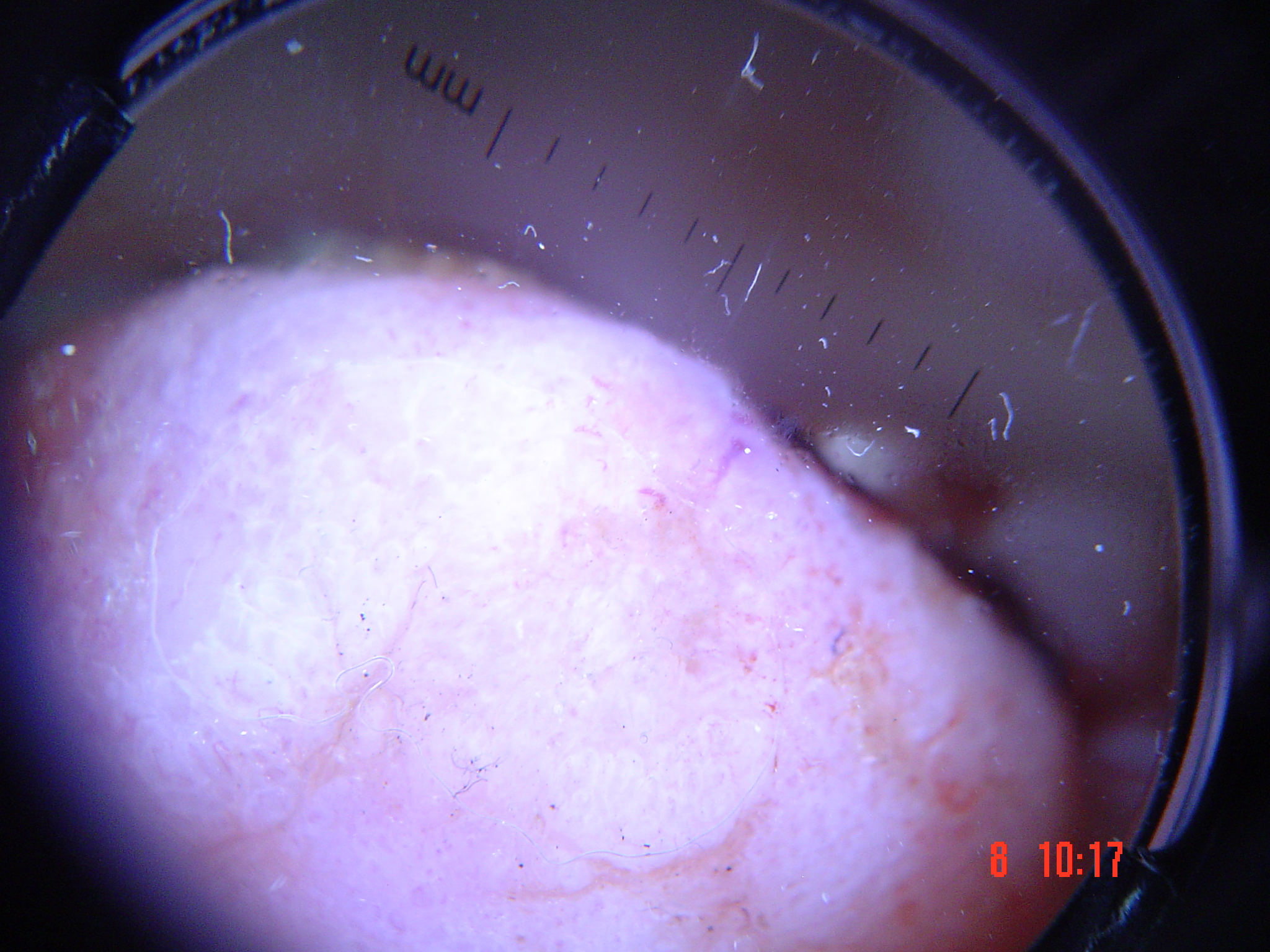imaging: dermoscopy, diagnosis: acral nodular melanoma (biopsy-proven).